The photograph was taken at an angle · the patient is female · the lesion involves the leg.
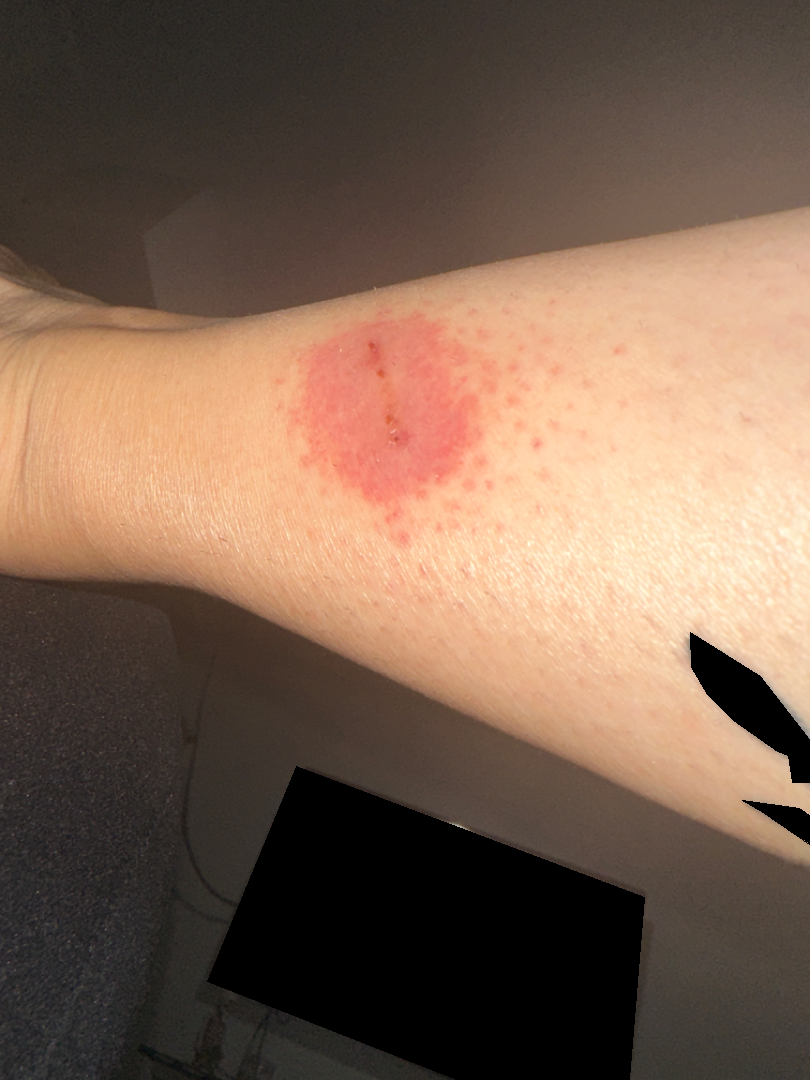Single-reviewer assessment: most likely Allergic Contact Dermatitis; also consider Irritant Contact Dermatitis.